A dermoscopy image of a single skin lesion: 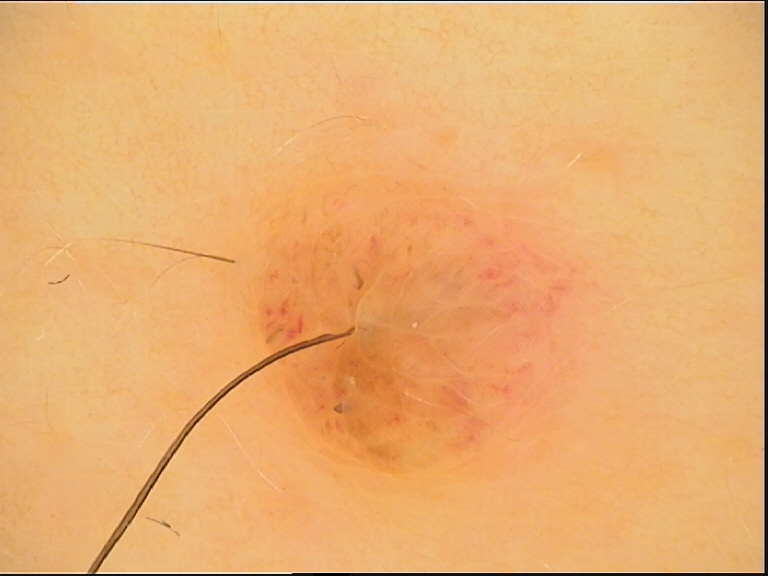The architecture is that of a banal lesion. The diagnostic label was a dermal nevus.